A dermatoscopic image of a skin lesion: 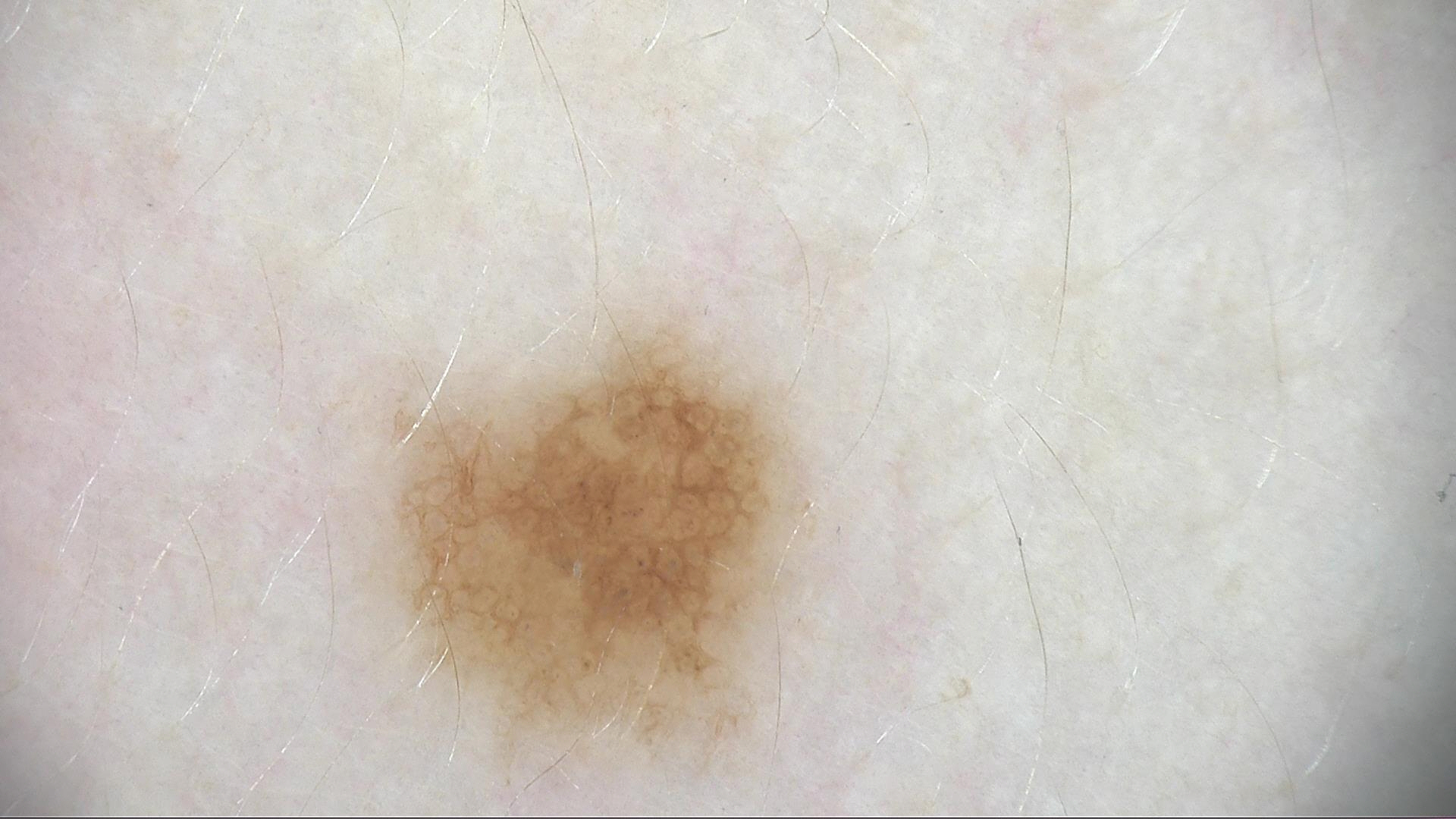Labeled as a dysplastic junctional nevus.